A female subject aged 28-32 · recorded as Fitzpatrick phototype III.
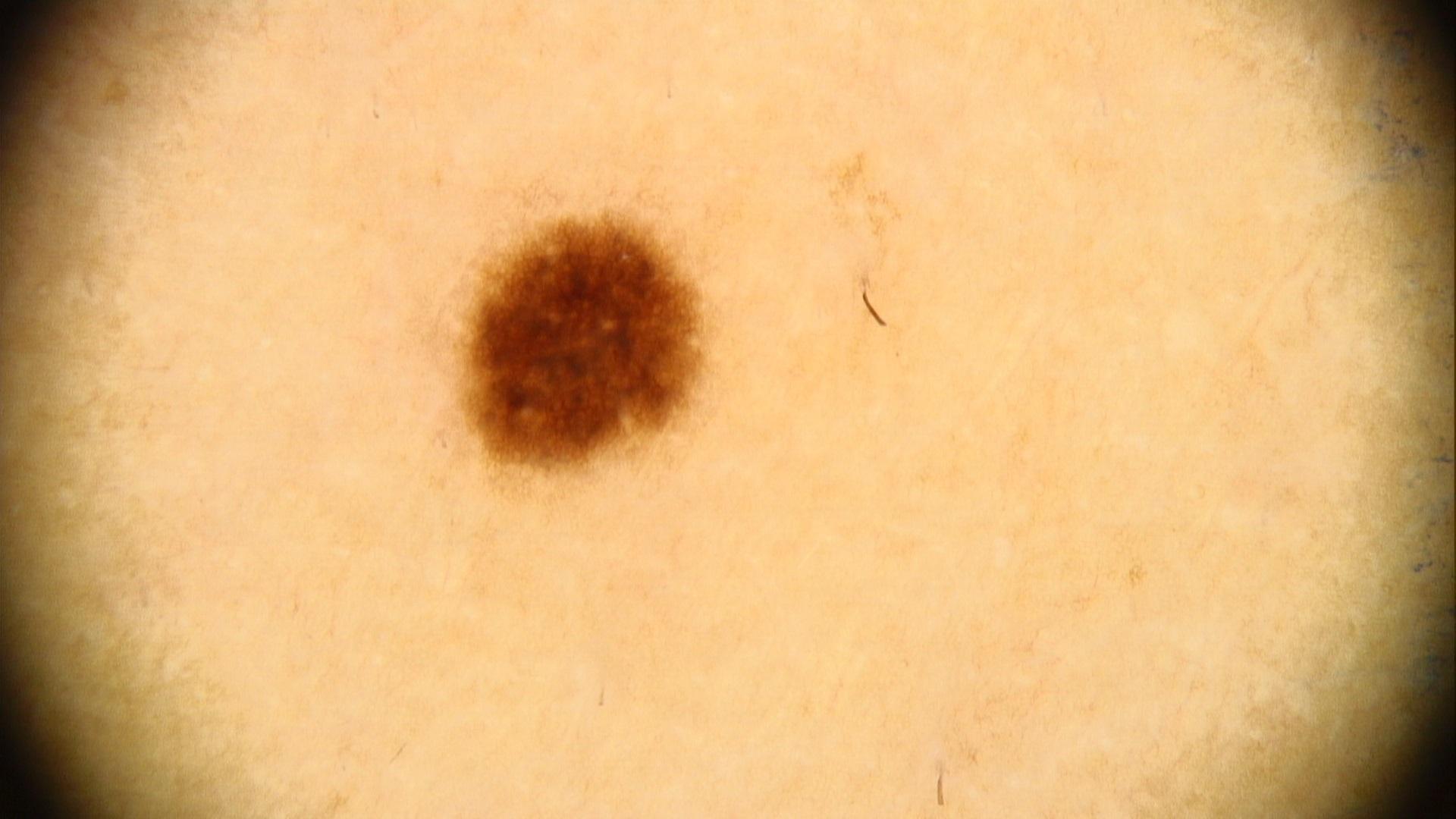anatomic site: a lower extremity | diagnostic label: Nevus (clinical impression).